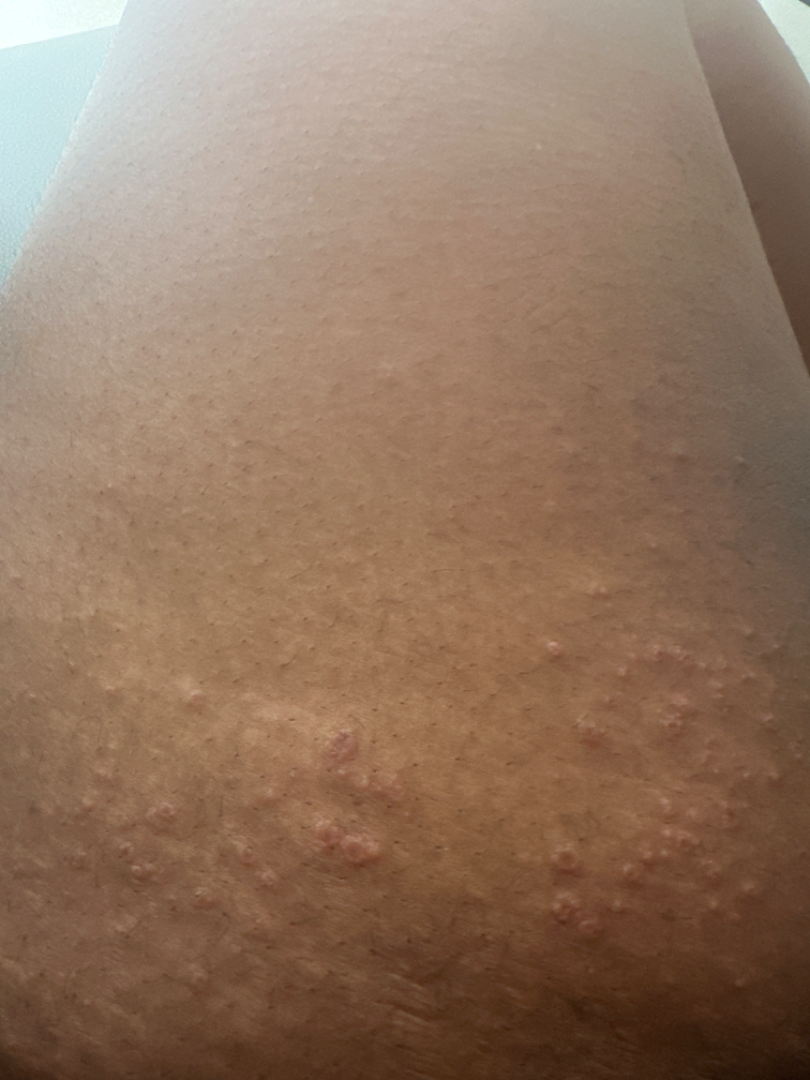| feature | finding |
|---|---|
| skin tone | Fitzpatrick V; non-clinician graders estimated MST 6 (US pool) or 4 (India pool) |
| image framing | close-up |
| diagnostic considerations | Impetigo, Herpes Zoster and Eczema were considered with similar weight |